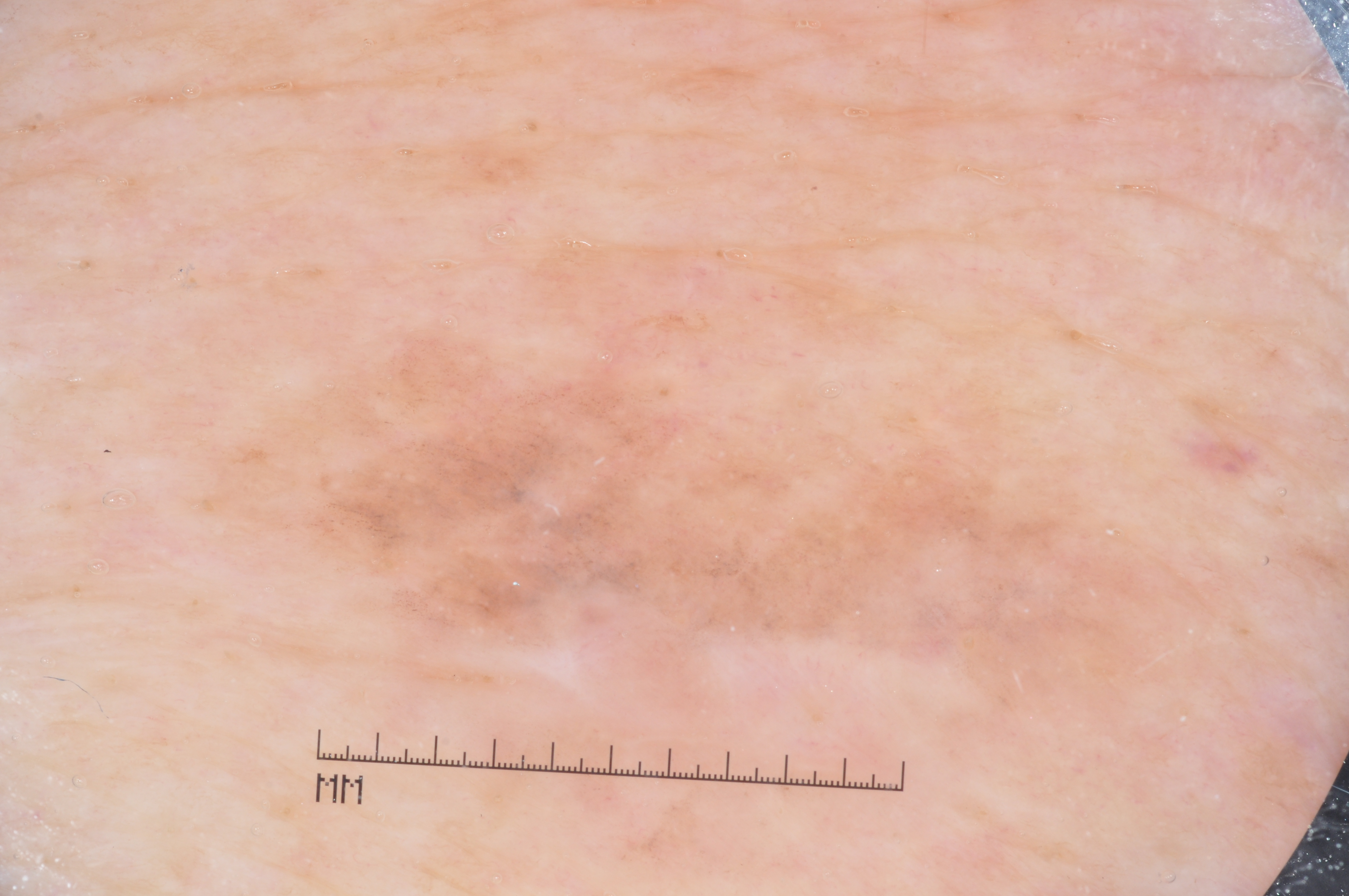{"image": {"modality": "dermoscopy"}, "patient": {"sex": "male", "age_approx": "85+"}, "dermoscopic_features": {"present": ["milia-like cysts"], "absent": ["negative network", "streaks", "pigment network"]}, "lesion_extent": "moderate", "lesion_location": {"bbox_xyxy": [189, 360, 1192, 715]}, "diagnosis": {"name": "melanoma", "malignancy": "malignant", "lineage": "melanocytic", "provenance": "histopathology"}}